The patient is 40–49, female · an image taken at a distance · the affected area is the front of the torso: 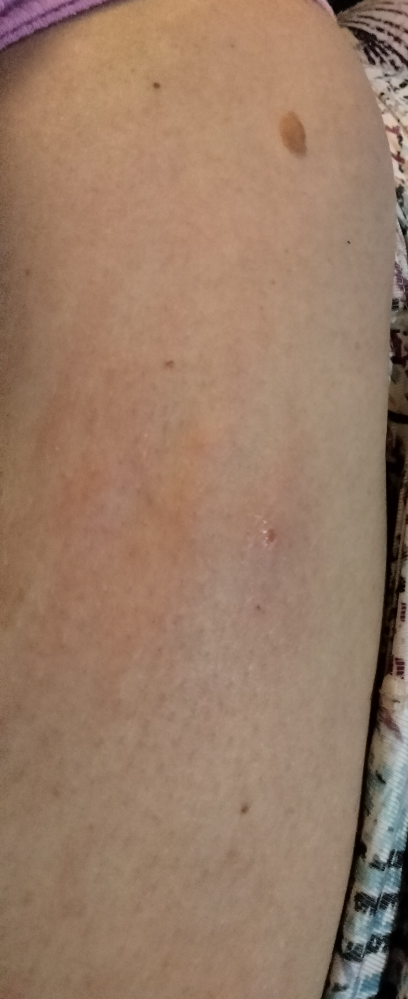| feature | finding |
|---|---|
| clinical impression | three dermatologists independently reviewed the case: most likely Folliculitis; less likely is Acne; a more distant consideration is Infected eczema; lower on the differential is Abscess |